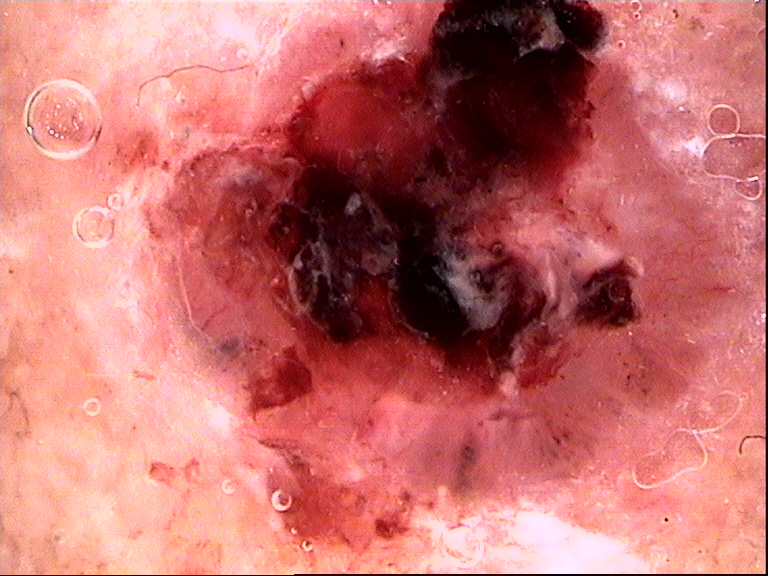diagnosis:
  name: basal cell carcinoma
  code: bcc
  malignancy: malignant
  super_class: non-melanocytic
  confirmation: histopathology